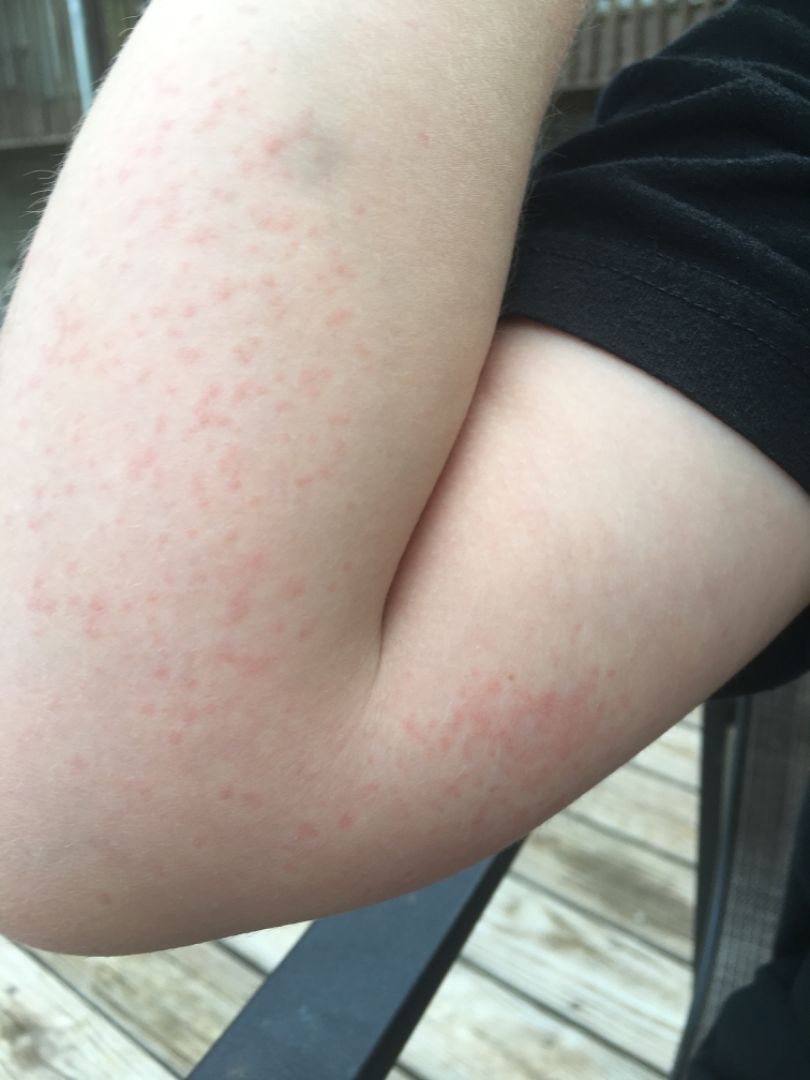The case was difficult to assess from the available photograph.
The photograph is a close-up of the affected area.